A clinical photograph of a skin lesion. Recorded as Fitzpatrick phototype III. A female subject age 47 — 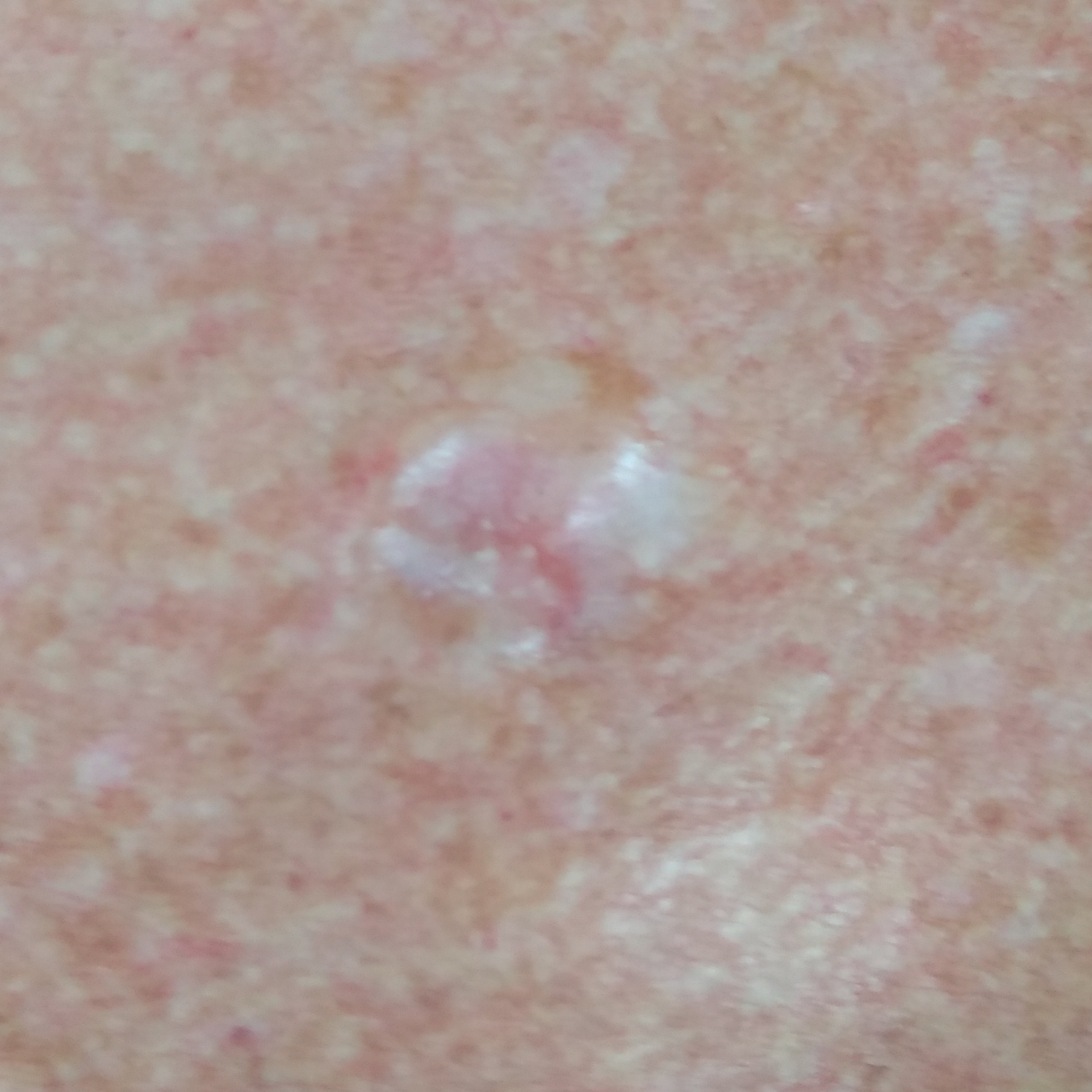Notes:
- region: the chest
- diameter: approx. 11 × 11 mm
- patient-reported symptoms: bleeding, elevation, growth, pain, itching / no change in appearance
- diagnosis: basal cell carcinoma (biopsy-proven)